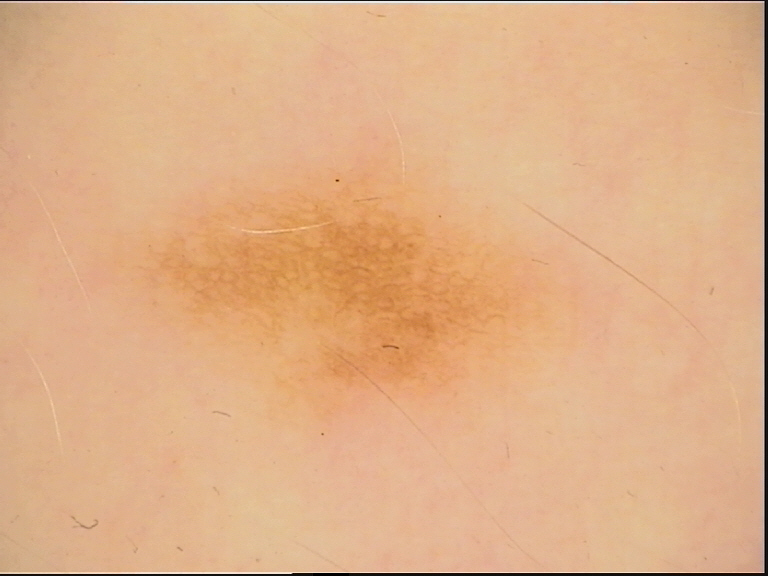Findings:
A dermoscopic image of a skin lesion. The architecture is that of a banal lesion.
Impression:
Labeled as a junctional nevus.